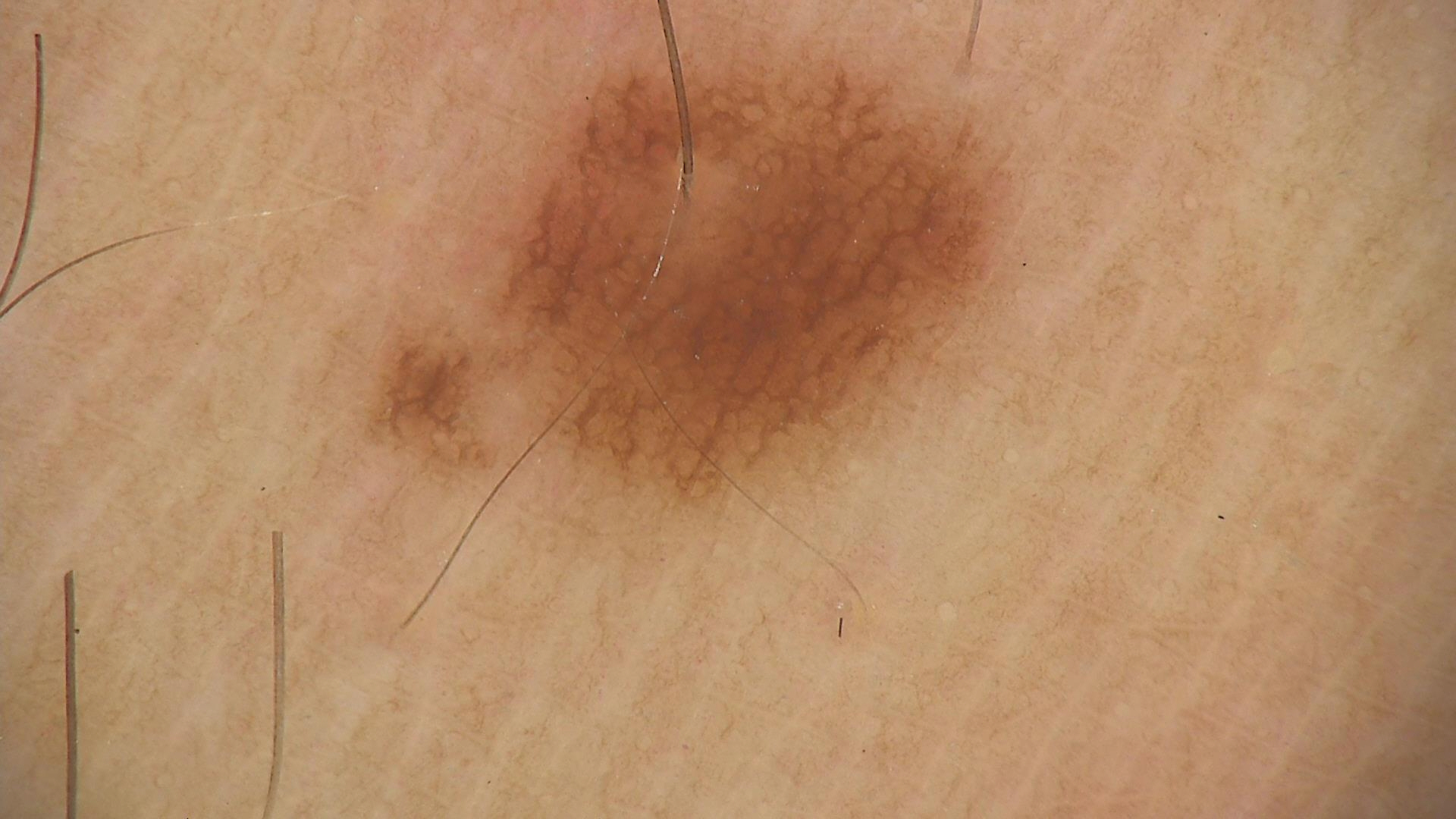Conclusion:
Classified as a banal lesion — a junctional nevus.